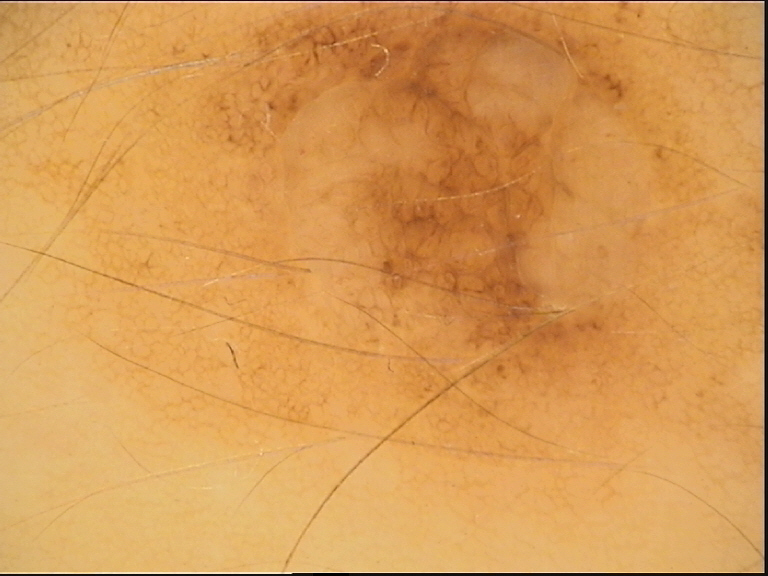<lesion>
<image>dermatoscopy</image>
<diagnosis>
<name>dermal nevus</name>
<code>db</code>
<malignancy>benign</malignancy>
<super_class>melanocytic</super_class>
<confirmation>expert consensus</confirmation>
</diagnosis>
</lesion>